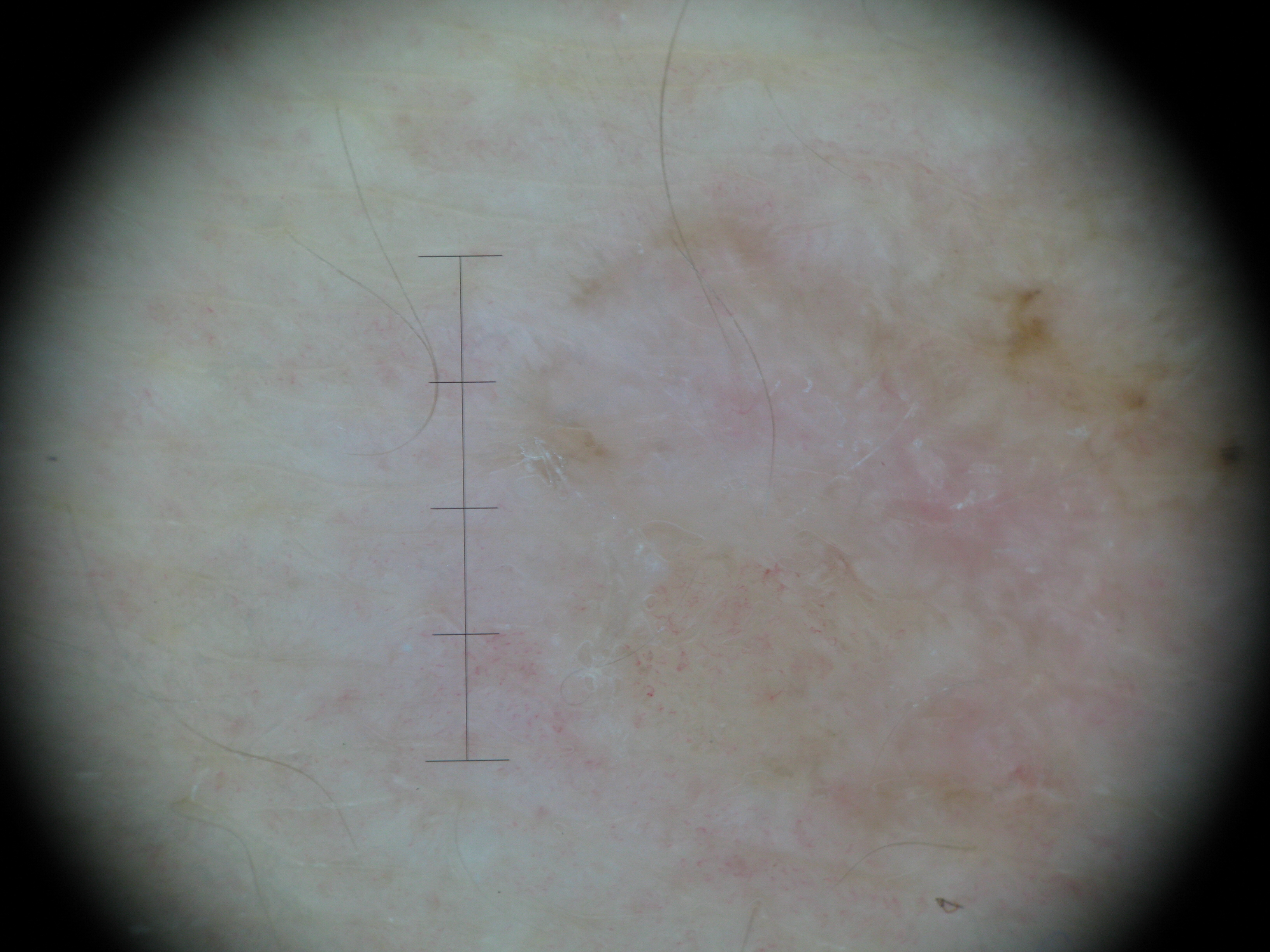The biopsy diagnosis was a keratinocytic, malignant lesion — a basal cell carcinoma.